The lesion involves the arm and front of the torso. The patient described the issue as a rash. This image was taken at an angle. The contributor reports the lesion is raised or bumpy. Reported lesion symptoms include itching. The condition has been present for less than one week:
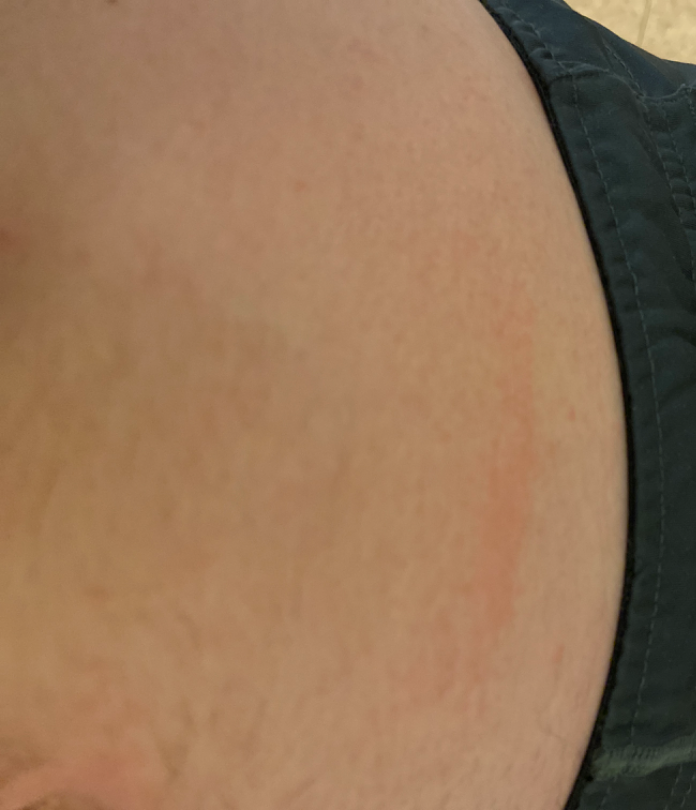The reviewing clinician's impression was: most consistent with Acute and chronic dermatitis.